The patient notes the condition has been present for less than one week; female contributor, age 18–29; a close-up photograph; texture is reported as raised or bumpy and rough or flaky: 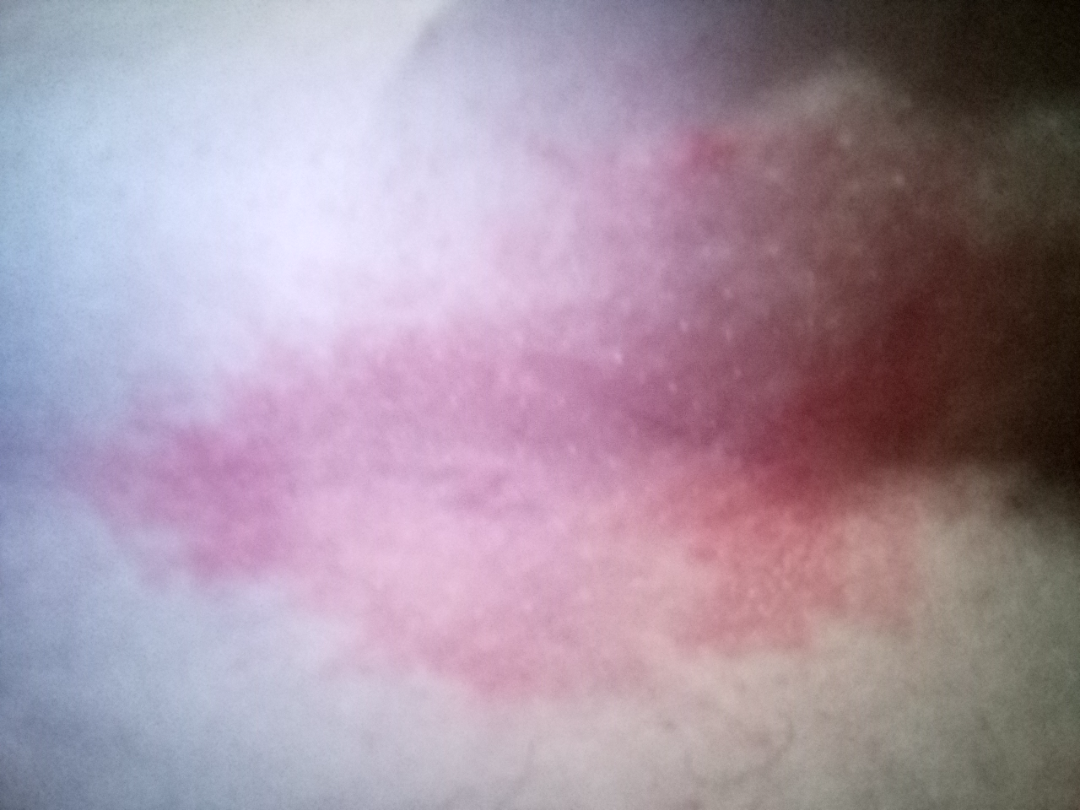One reviewing dermatologist: Inverse psoriasis, Candida intertrigo and Seborrheic Dermatitis were considered with similar weight.